An image taken at an angle.
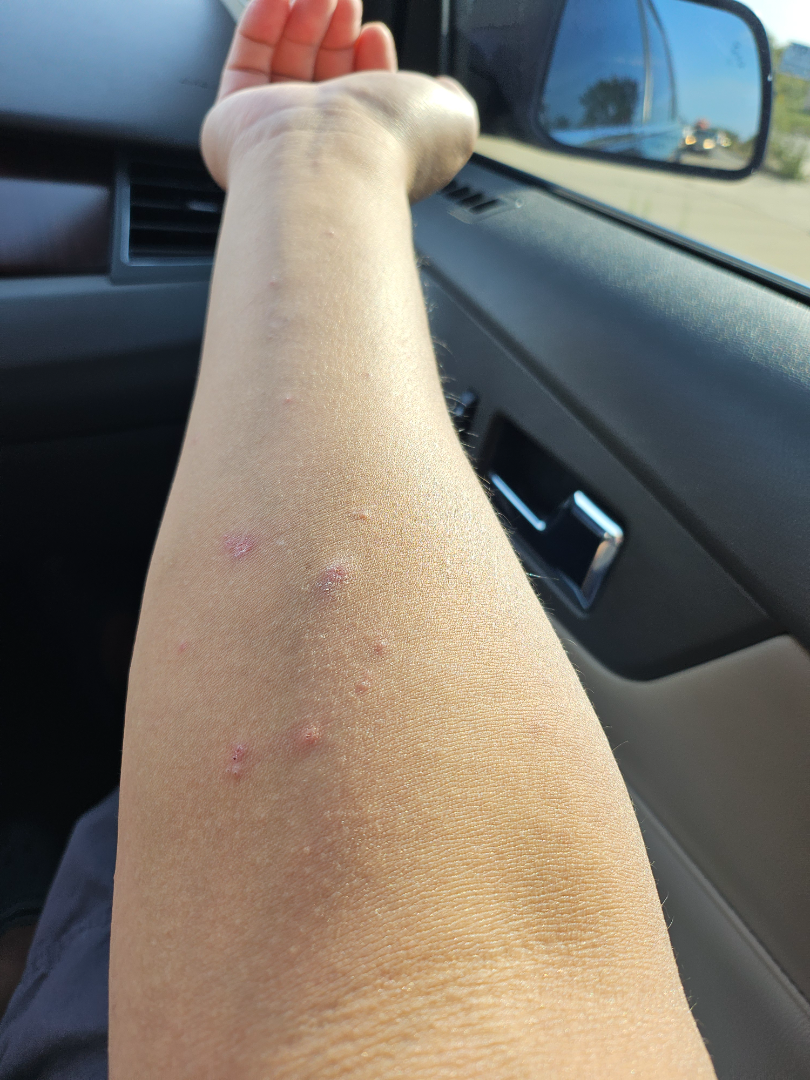On photographic review by a dermatologist: most likely Lichen planus/lichenoid eruption; possibly Eczema; also consider Insect Bite.